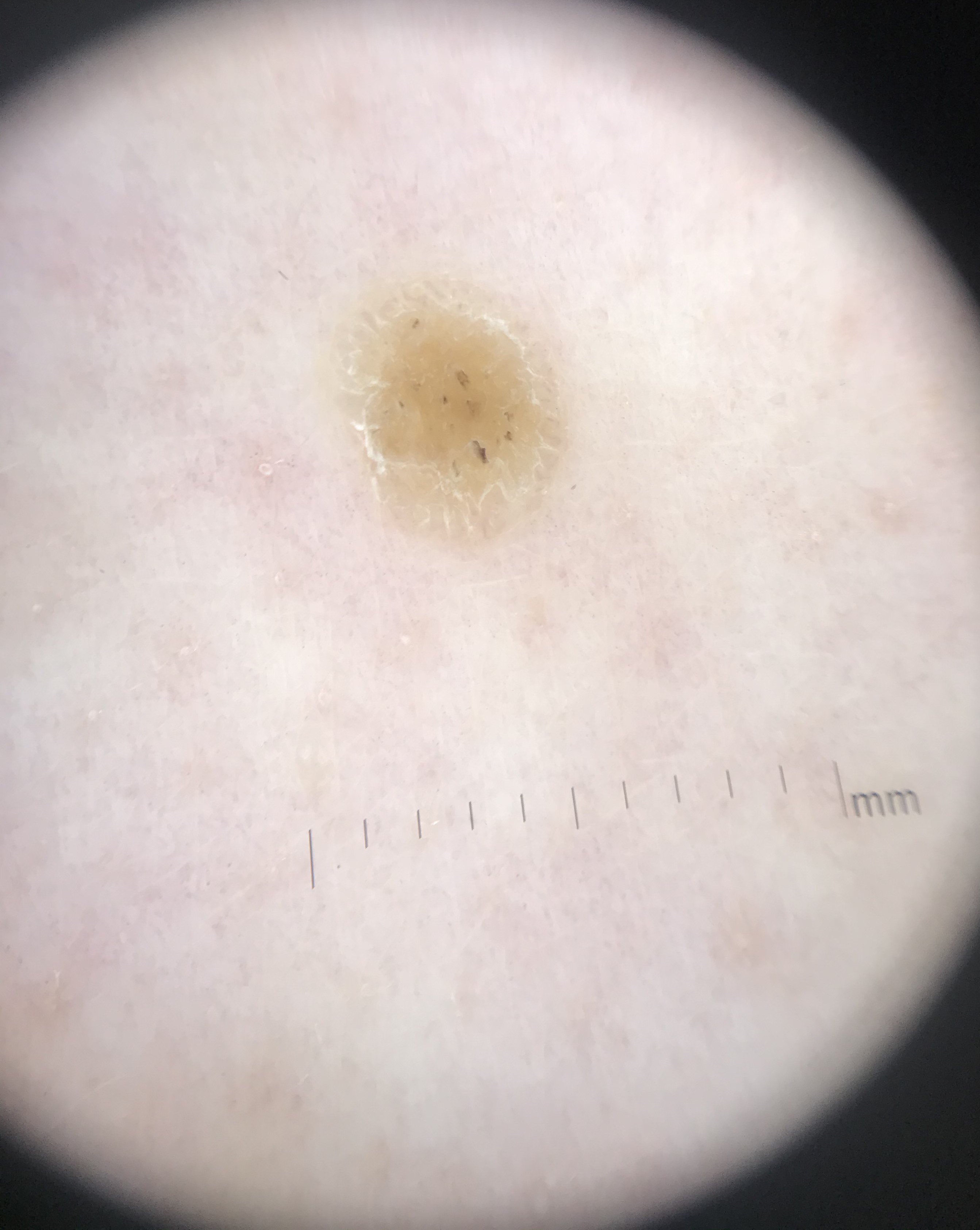<dermoscopy>
  <diagnosis>
    <name>seborrheic keratosis</name>
    <code>sk</code>
    <malignancy>benign</malignancy>
    <super_class>non-melanocytic</super_class>
    <confirmation>expert consensus</confirmation>
  </diagnosis>
</dermoscopy>